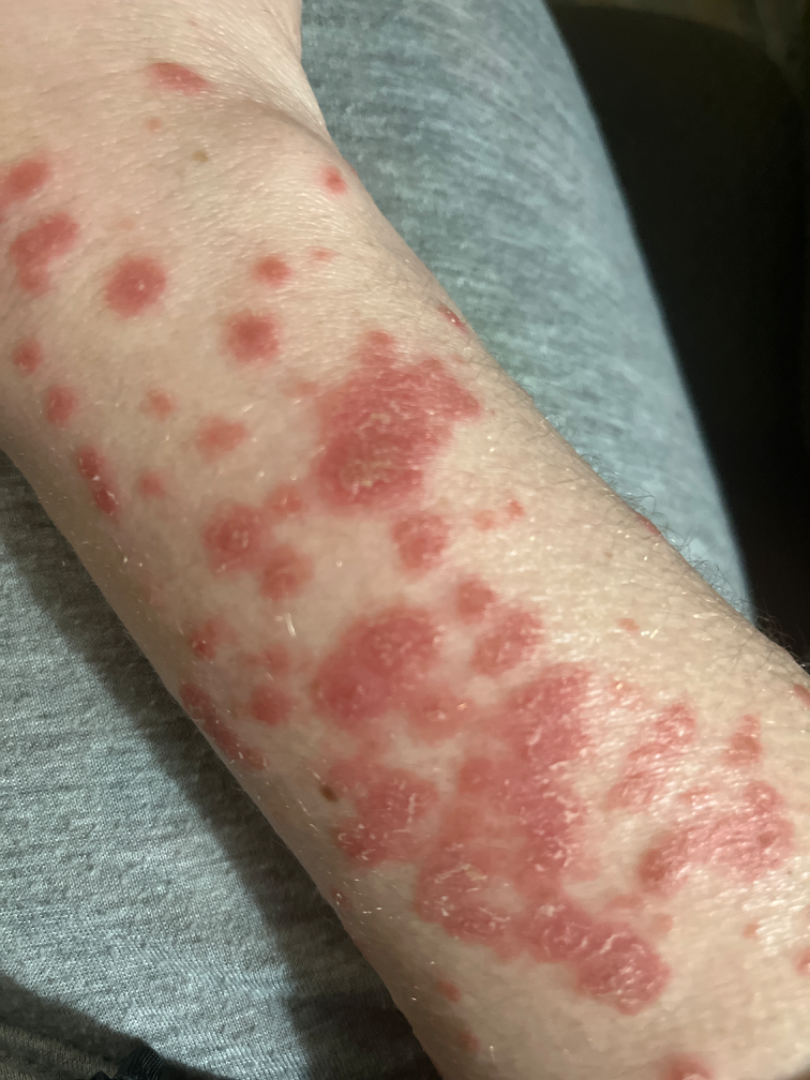On teledermatology review: consistent with Erythema multiforme.